A dermoscopy image of a single skin lesion.
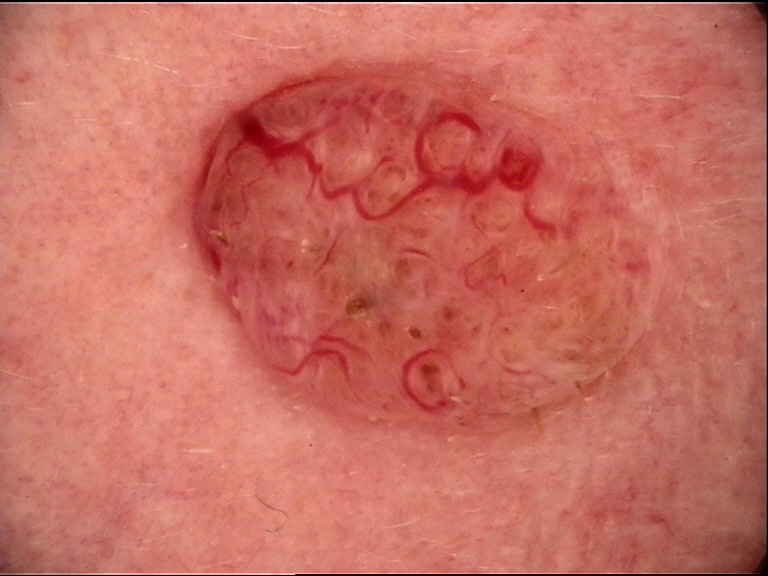Q: What did the workup show?
A: basal cell carcinoma (biopsy-proven)